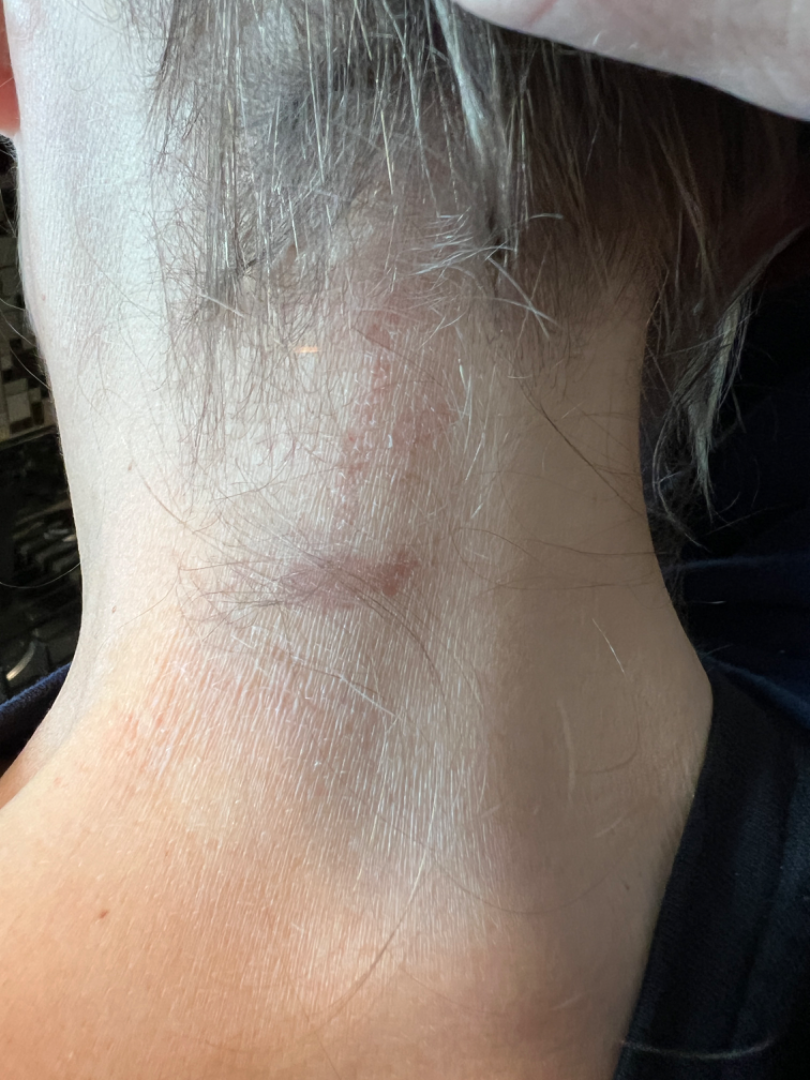Located on the head or neck.
This is a close-up image.
On dermatologist assessment of the image: Psoriasis, Eczema and Seborrheic Dermatitis were each considered, in no particular order.